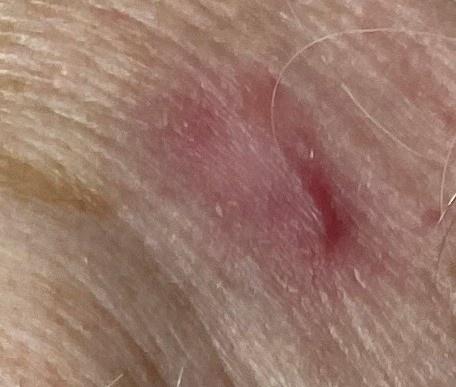Image and clinical context: Recorded as Fitzpatrick skin type I. Per the chart, no previous melanoma and no first-degree relative with melanoma. Conclusion: Confirmed on histopathology as a squamous cell carcinoma.